The chart documents a prior melanoma. A clinical photograph showing a skin lesion in context. FST III.
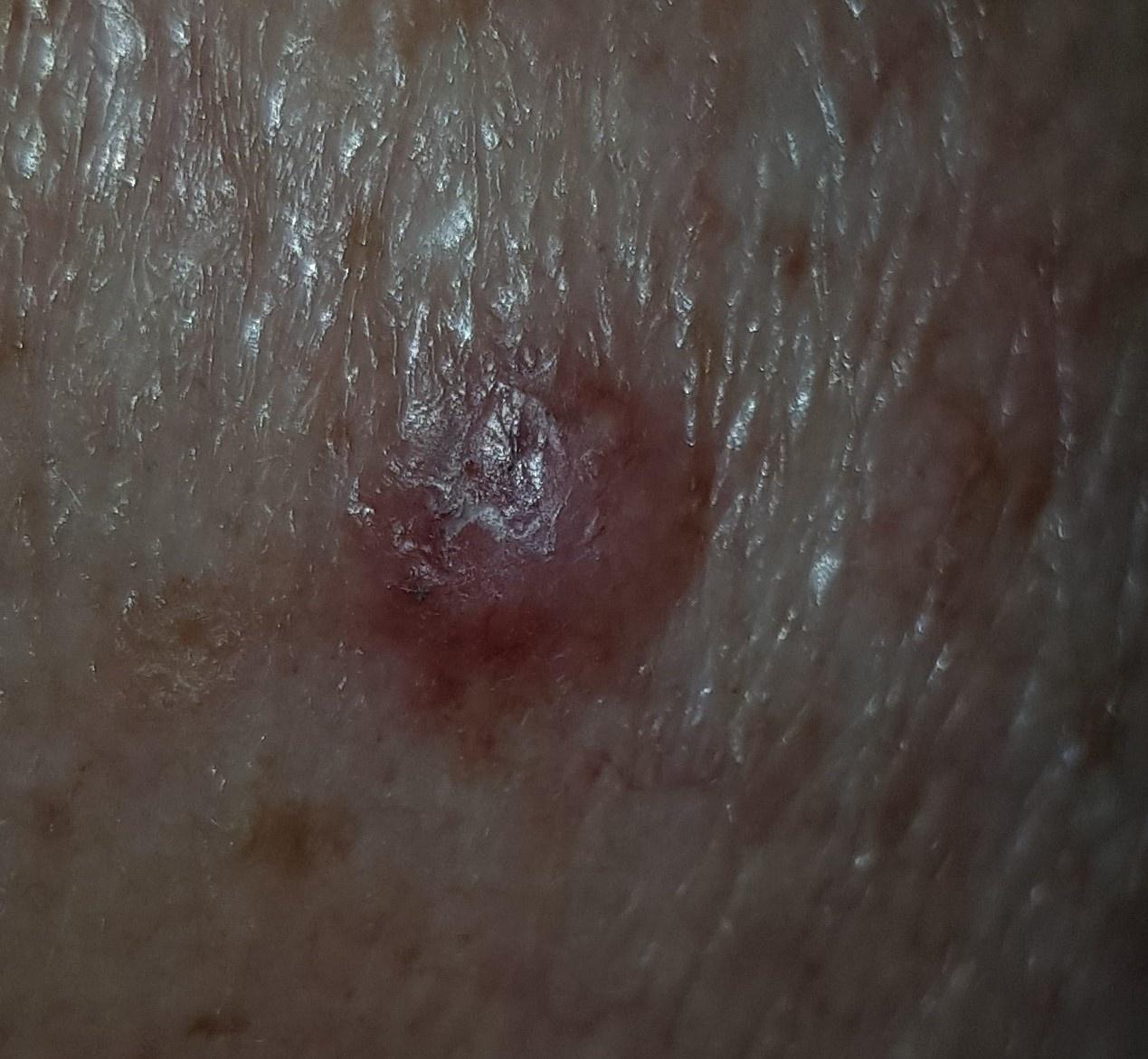The biopsy diagnosis was a basal cell carcinoma.